The photograph was taken at a distance; the contributor is a female aged 70–79; the arm is involved: 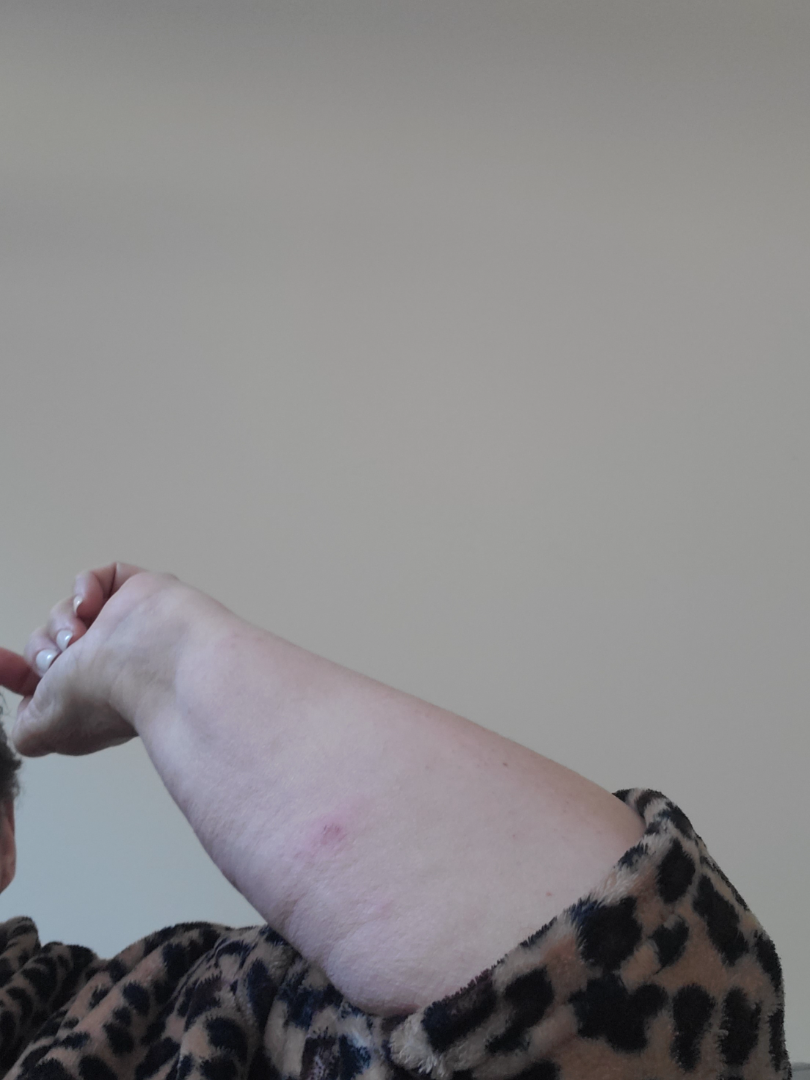{"assessment": "not assessable"}